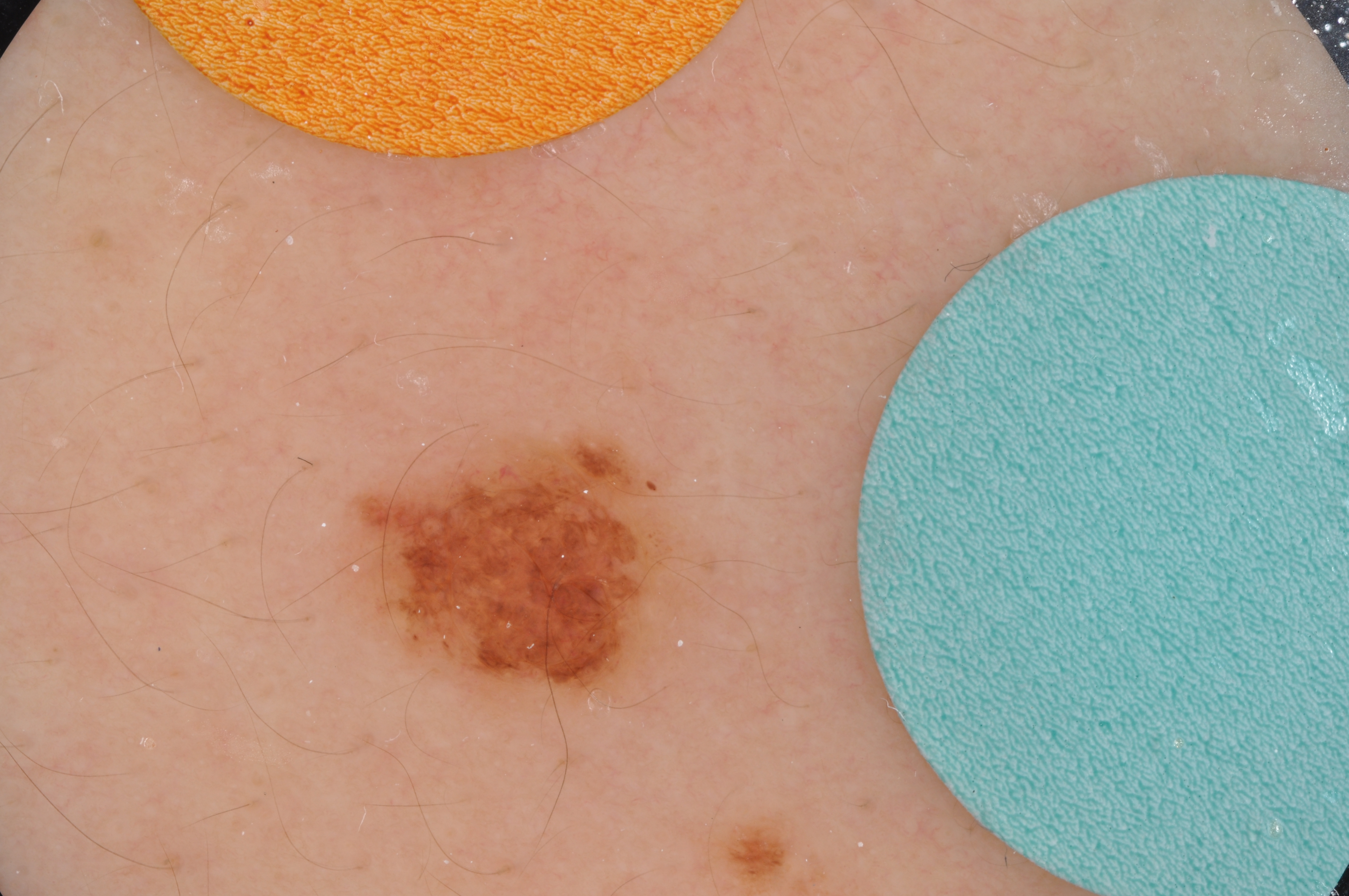Image and clinical context:
The patient is a male aged approximately 15. A dermoscopy image of a single skin lesion. On dermoscopy, the lesion shows no negative network, pigment network, milia-like cysts, streaks, or globules. The lesion is located at x1=331, y1=426, x2=702, y2=721. The lesion occupies roughly 7% of the field.
Impression:
Consistent with a melanocytic nevus, a benign lesion.